An image taken at an angle · the contributor is 50–59, male · the lesion involves the leg — 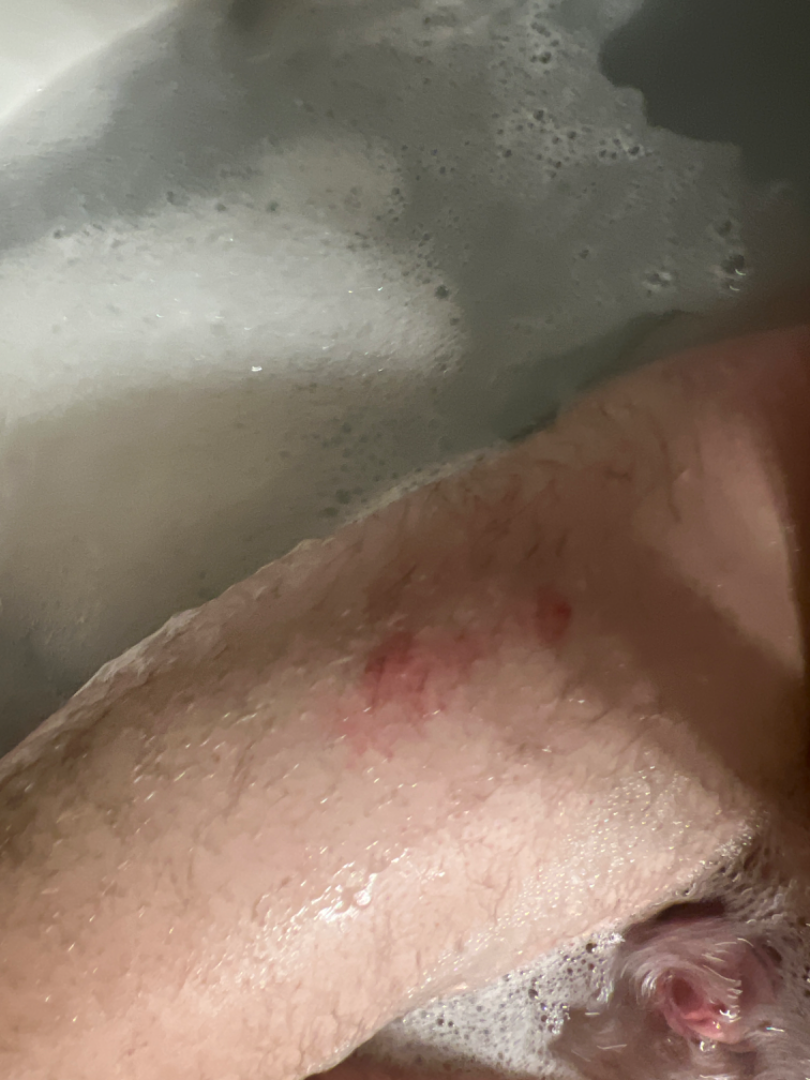Most consistent with Allergic Contact Dermatitis; also raised was Insect Bite; lower on the differential is Eczema.